A dermoscopic close-up of a skin lesion:
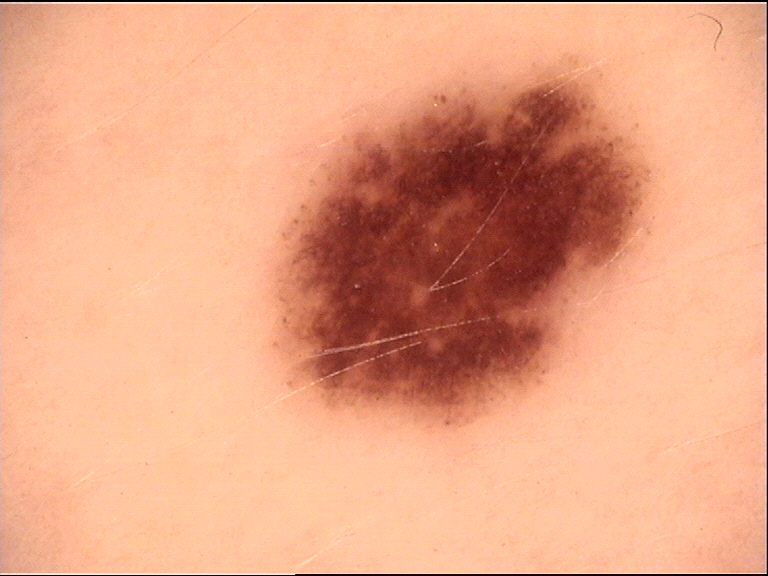Diagnosed as a benign lesion — a dysplastic junctional nevus.